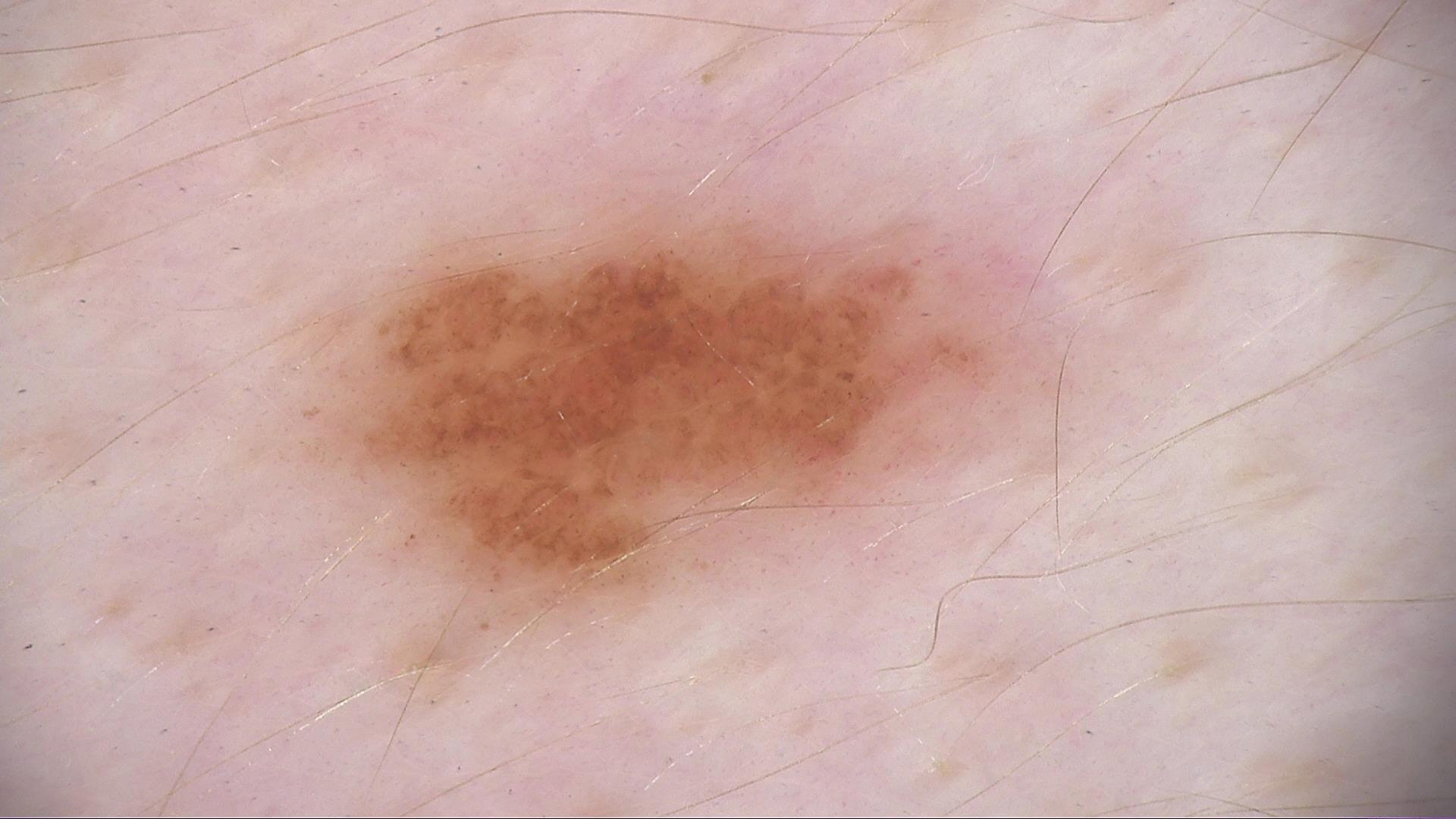image = dermatoscopy; class = dysplastic junctional nevus (expert consensus).